The subject is 30–39, male · the affected area is the arm · close-up view — 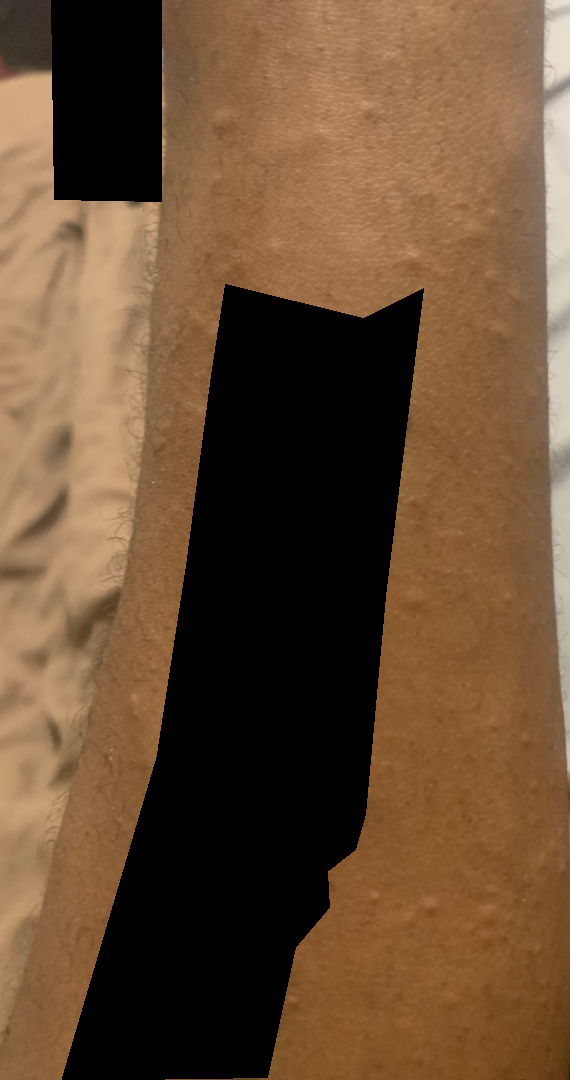Assessment: Most consistent with Lichenoid myxedema; an alternative is Clinical neurofibromatosis.